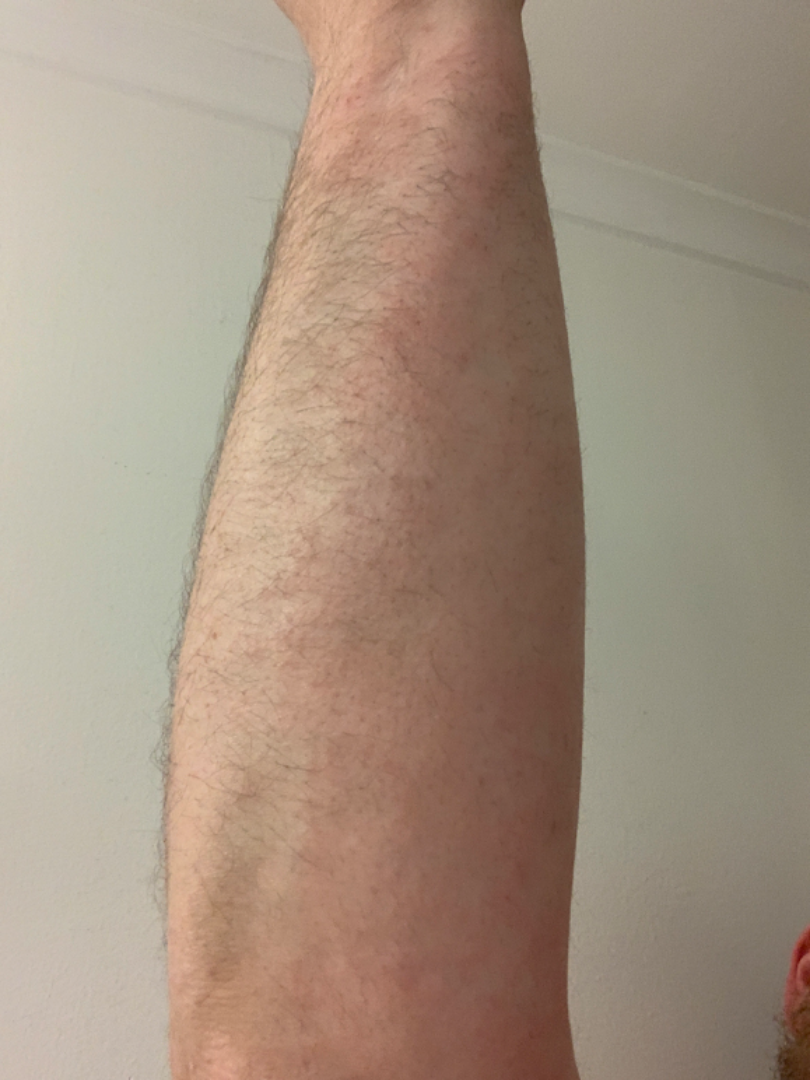The case was difficult to assess from the available photograph.
The affected area is the arm and leg.
The patient also reports chills, fatigue and shortness of breath.
Texture is reported as raised or bumpy.
The condition has been present for less than one week.
The photograph was taken at a distance.
Symptoms reported: enlargement, itching, burning and pain.
The patient described the issue as a rash.